A skin lesion imaged with a dermatoscope.
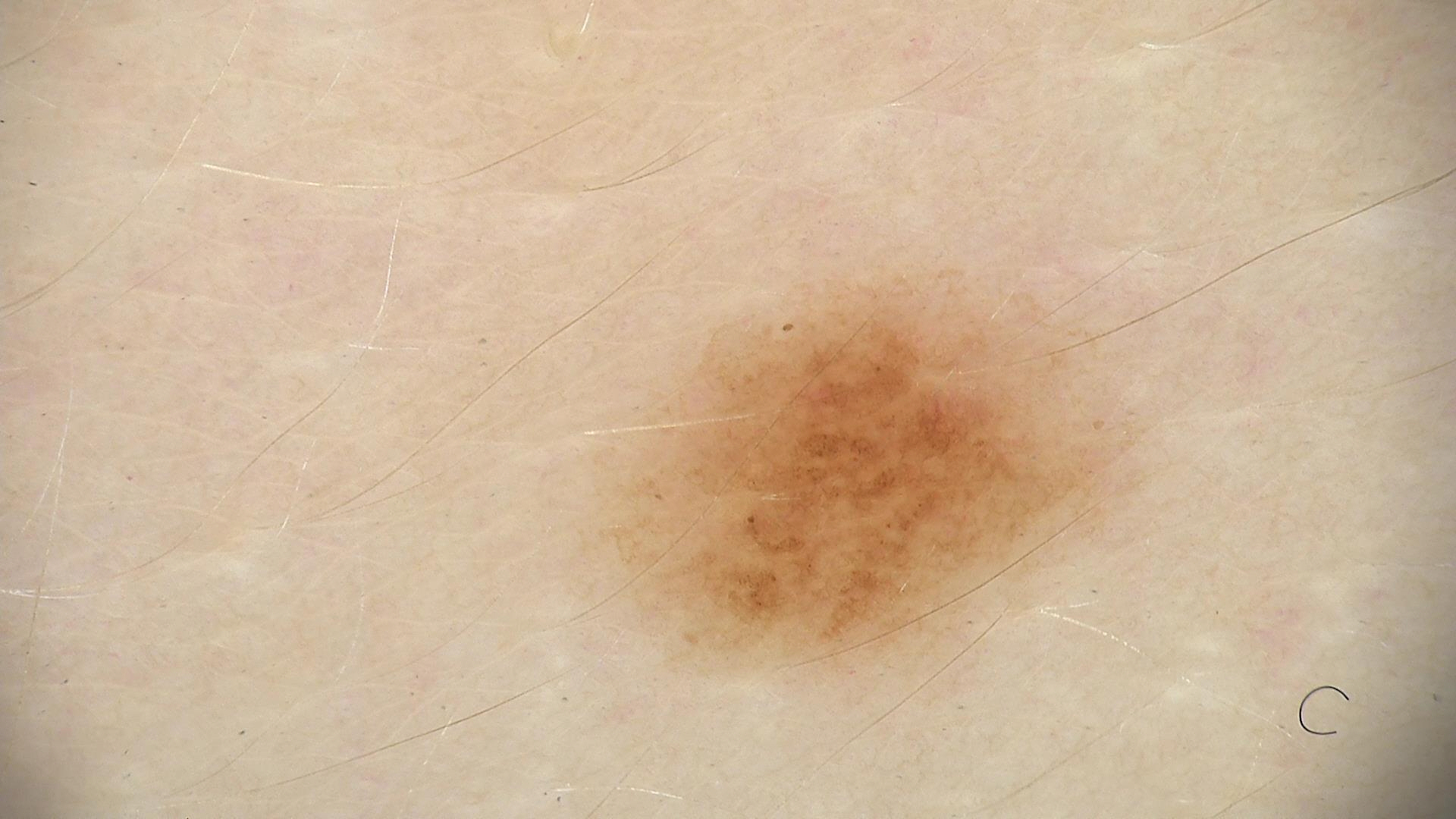Classified as a benign lesion — a dysplastic junctional nevus.